The photo was captured at a distance · female subject, age 30–39 · located on the arm.
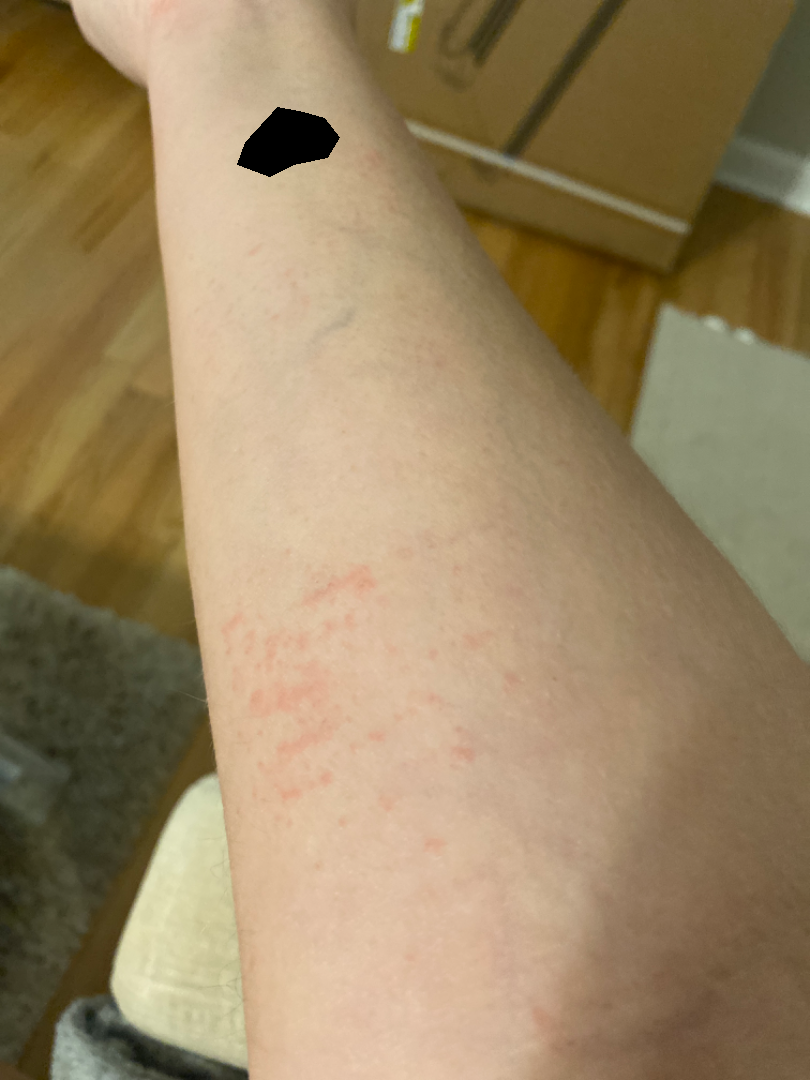Findings: Single-reviewer assessment: the reviewer's impression was Acute dermatitis, NOS.